A skin lesion imaged with a dermatoscope:
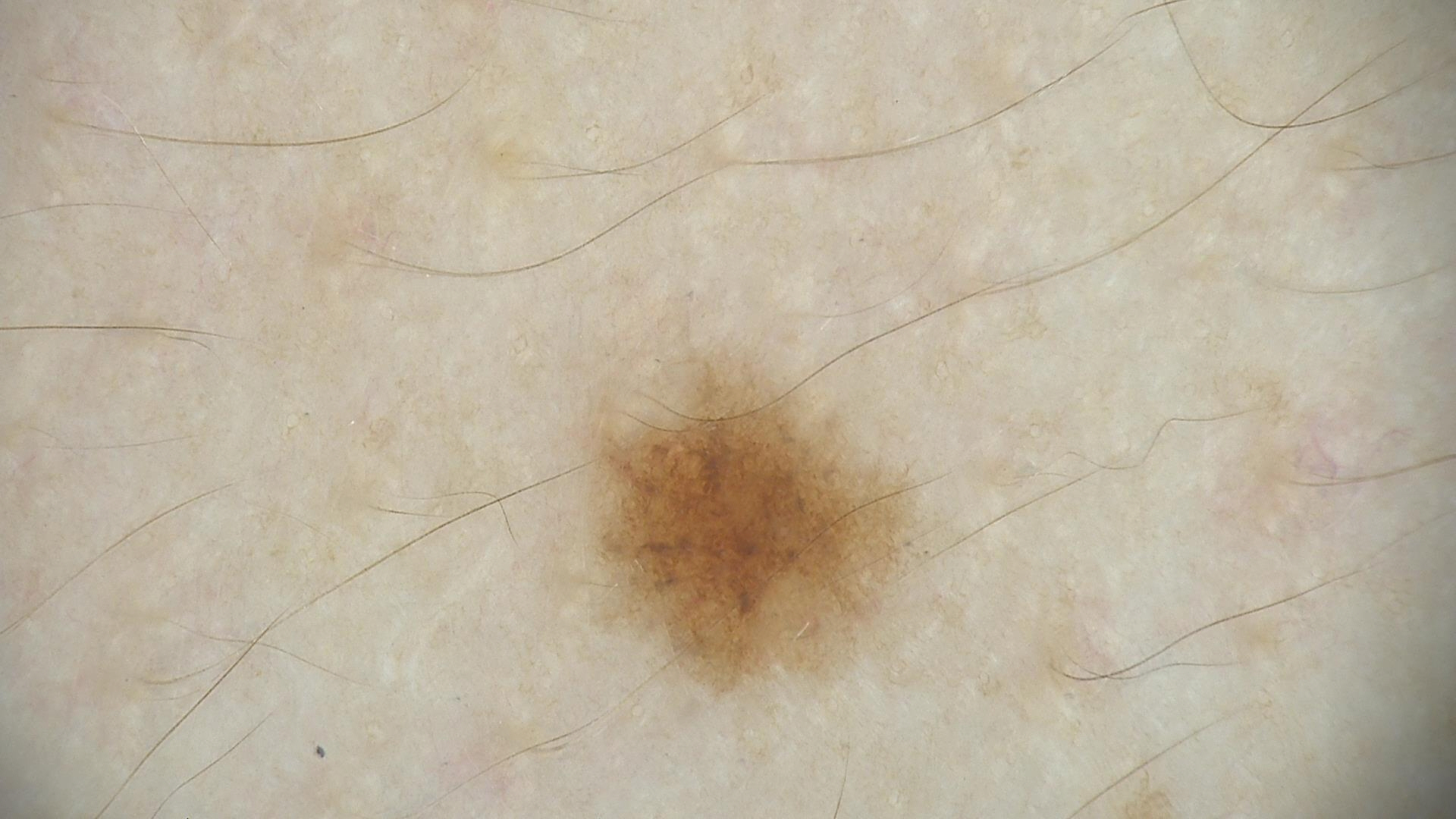diagnosis — dysplastic junctional nevus (expert consensus).